A dermatoscopic image of a skin lesion: 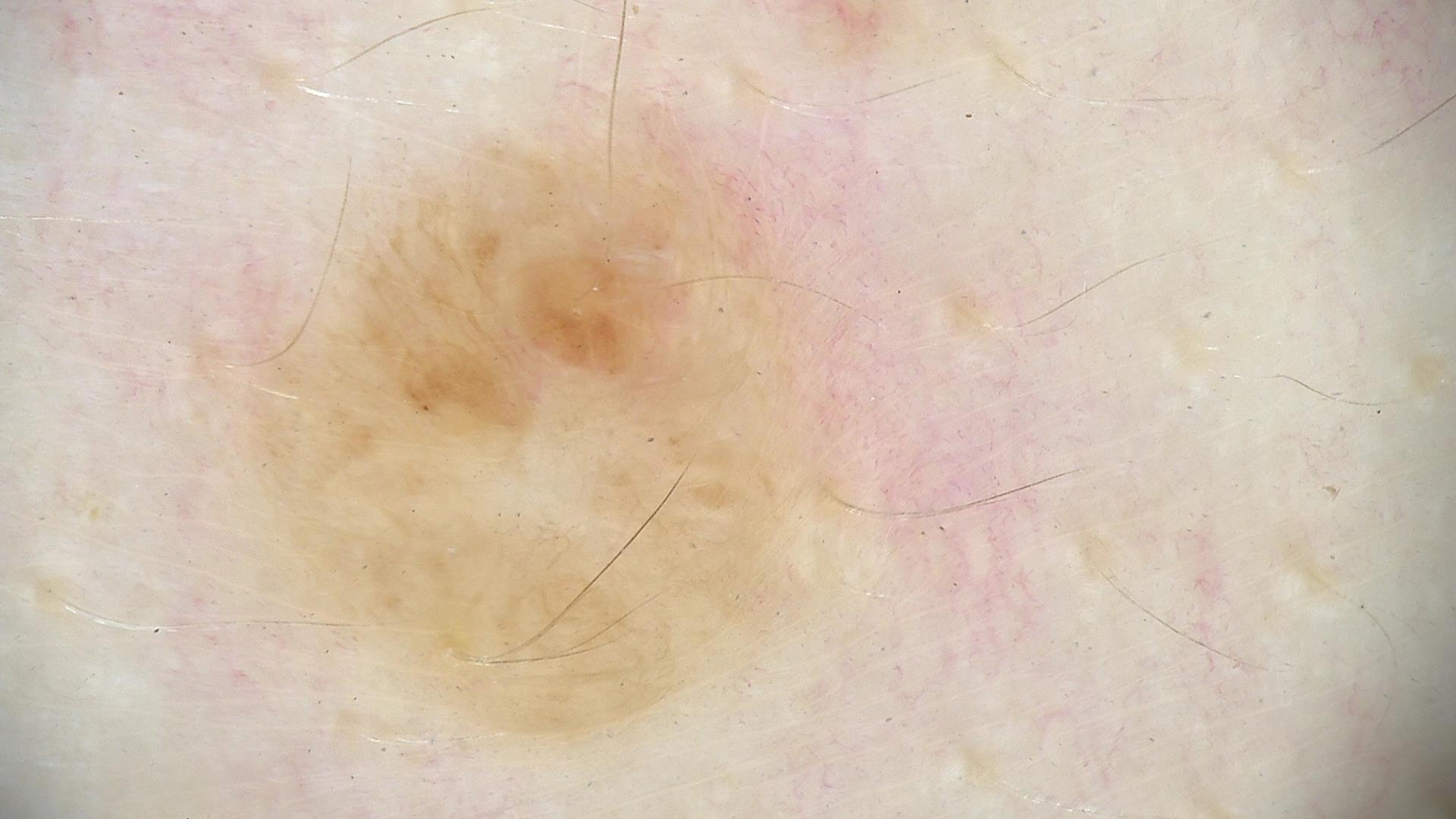Impression: Consistent with a banal lesion — a dermal nevus.